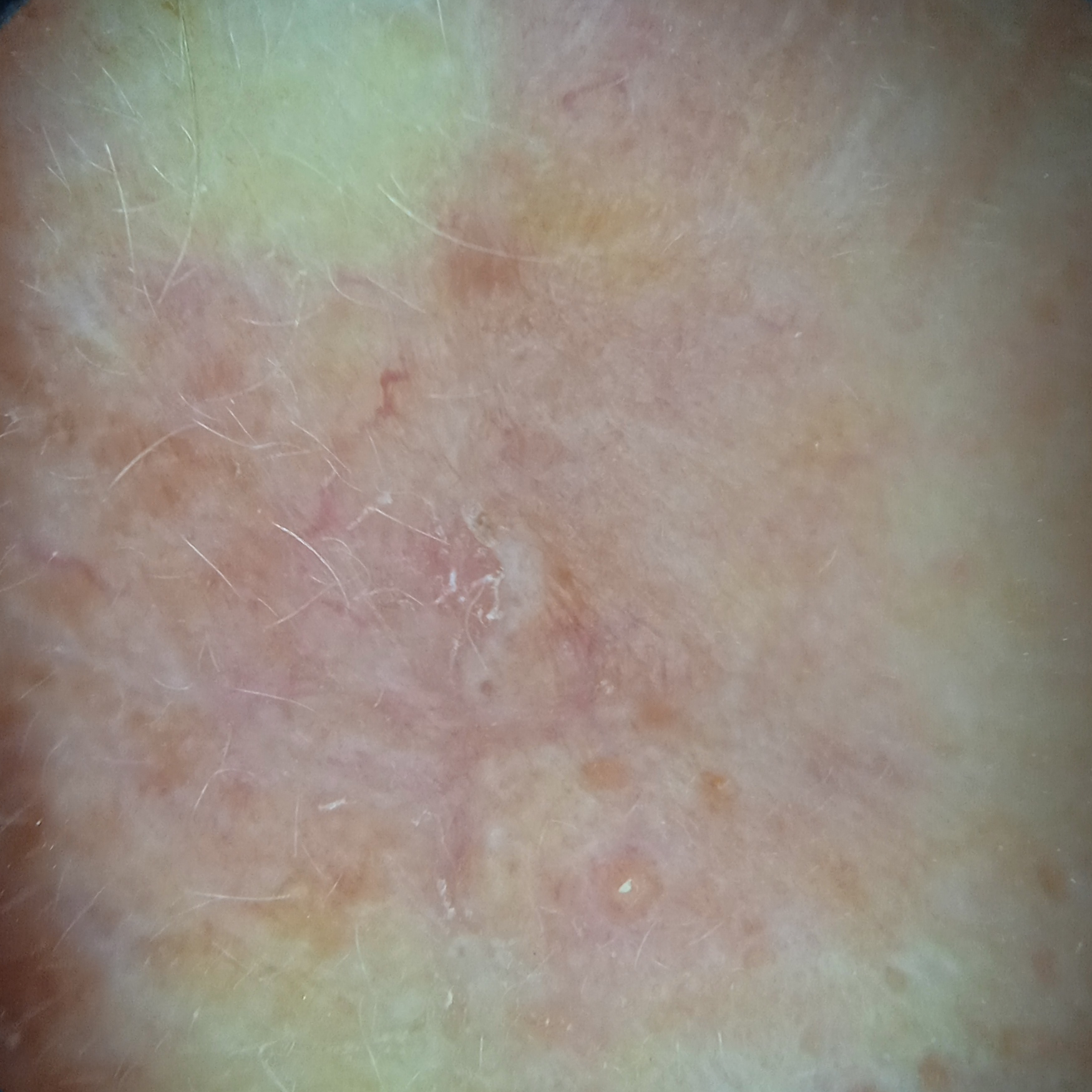Imaged for a research study, with no referral diagnosis recorded. Few moles overall by the patient's own estimate. A skin lesion imaged with a dermatoscope. A female patient 68 years old. The lesion is located on the face. The lesion is about 9.9 mm across. The lesion was assessed as an actinic keratosis.